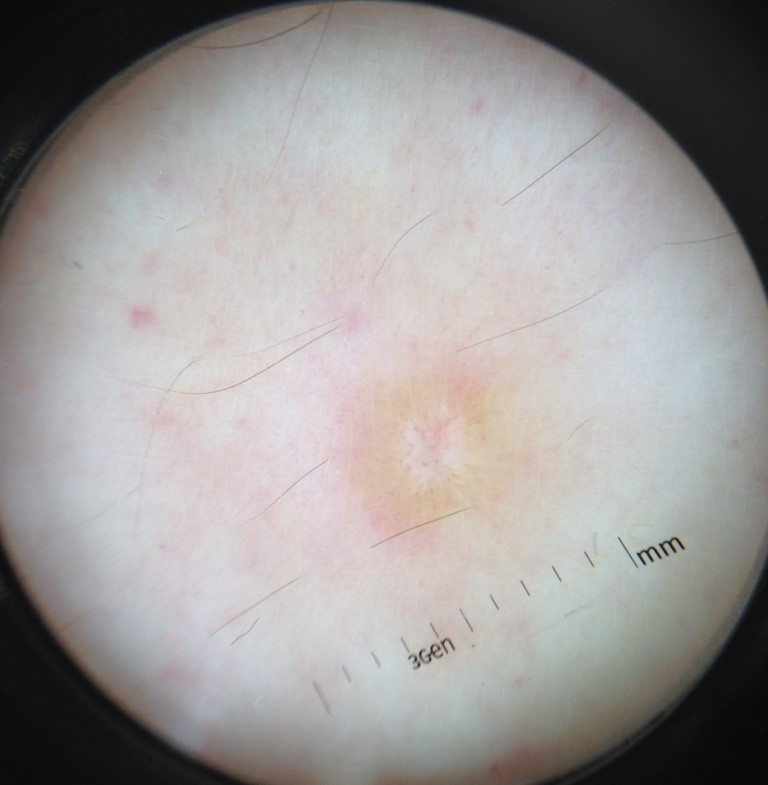| field | value |
|---|---|
| image type | dermoscopy |
| diagnosis | dermatofibroma (expert consensus) |